A dermoscopic close-up of a skin lesion, a female subject roughly 60 years of age: 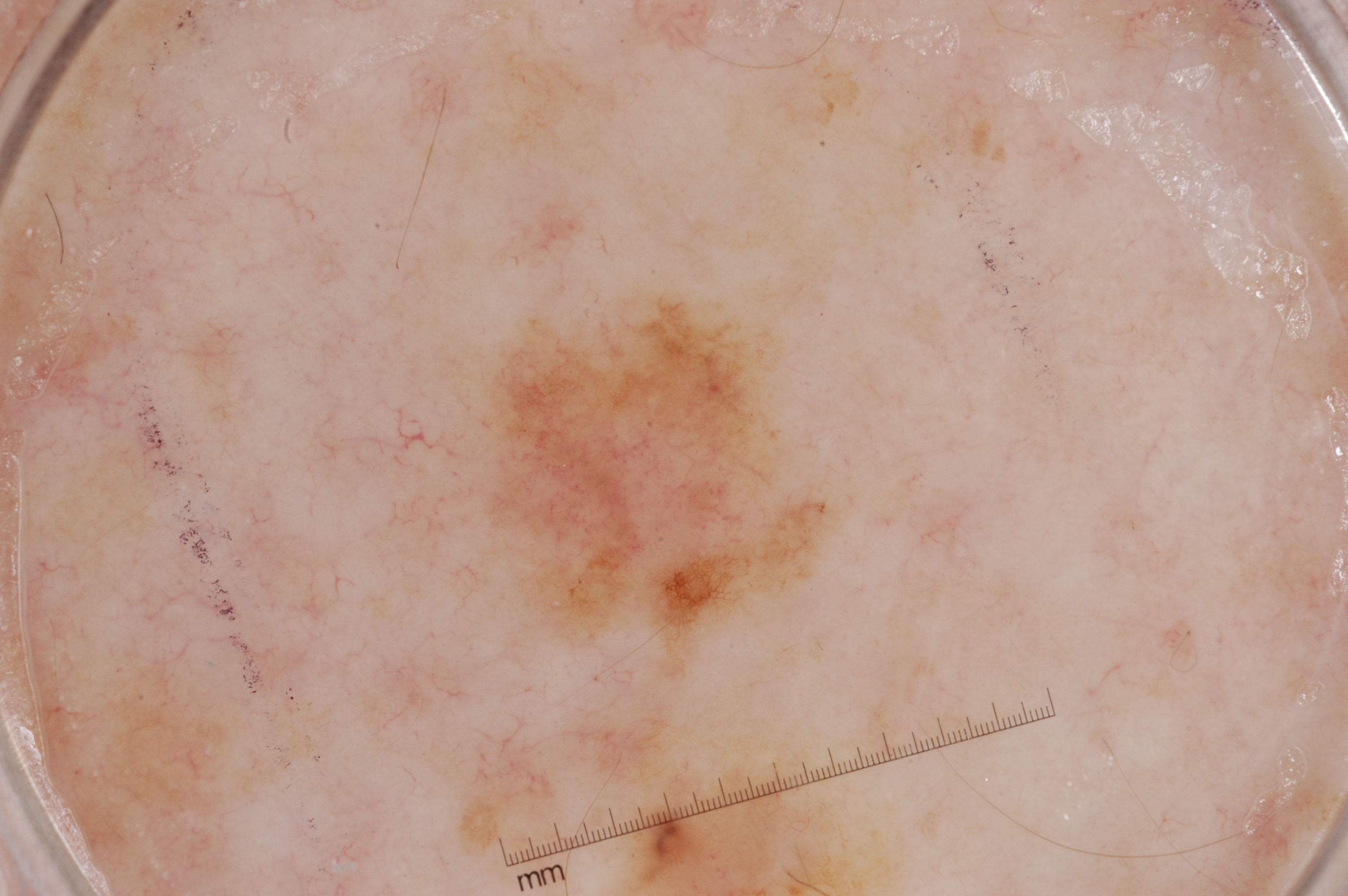Findings: The lesion covers approximately 11% of the dermoscopic field. On dermoscopy, the lesion shows pigment network and milia-like cysts, with no negative network or streaks. As (left, top, right, bottom), lesion location: box(447, 262, 846, 682). Conclusion: Histopathological examination showed a melanoma.